A subject 72 years old.
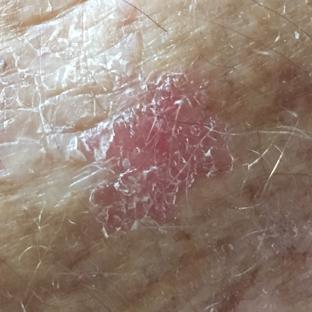symptoms: itching / no change in appearance, no pain | diagnosis: actinic keratosis (clinical consensus).